Dermoscopy of a skin lesion: 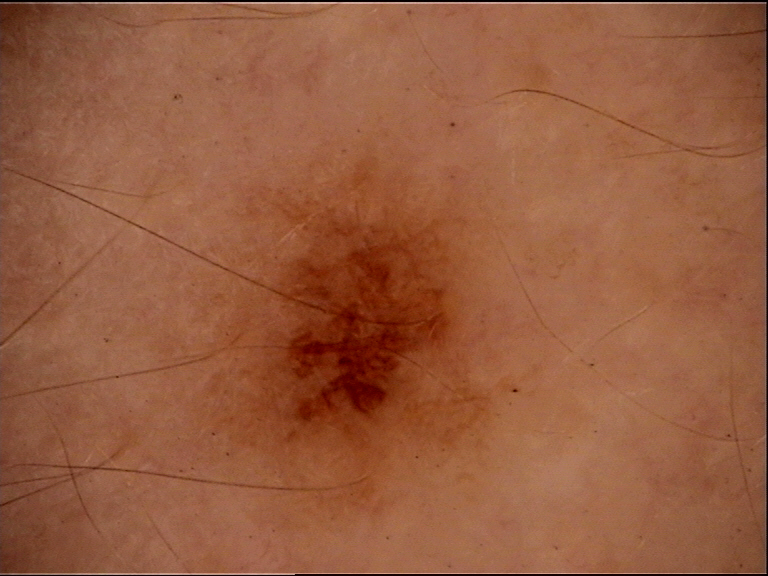The diagnostic label was a dysplastic junctional nevus.